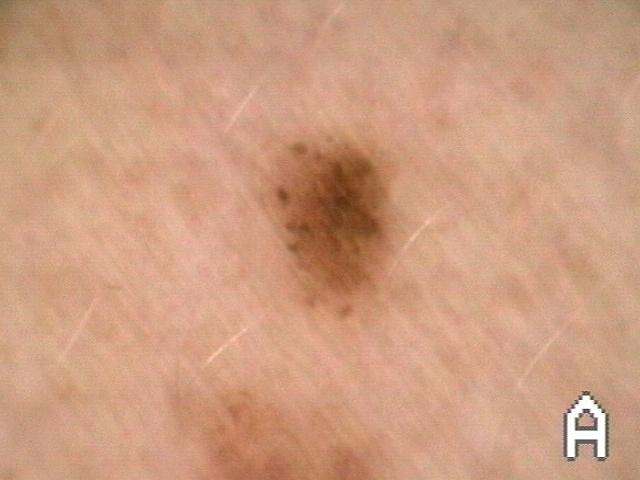Case summary:
A female subject aged 48-52. The lesion was found on the trunk (the posterior trunk).
Assessment:
The clinical impression was a nevus.